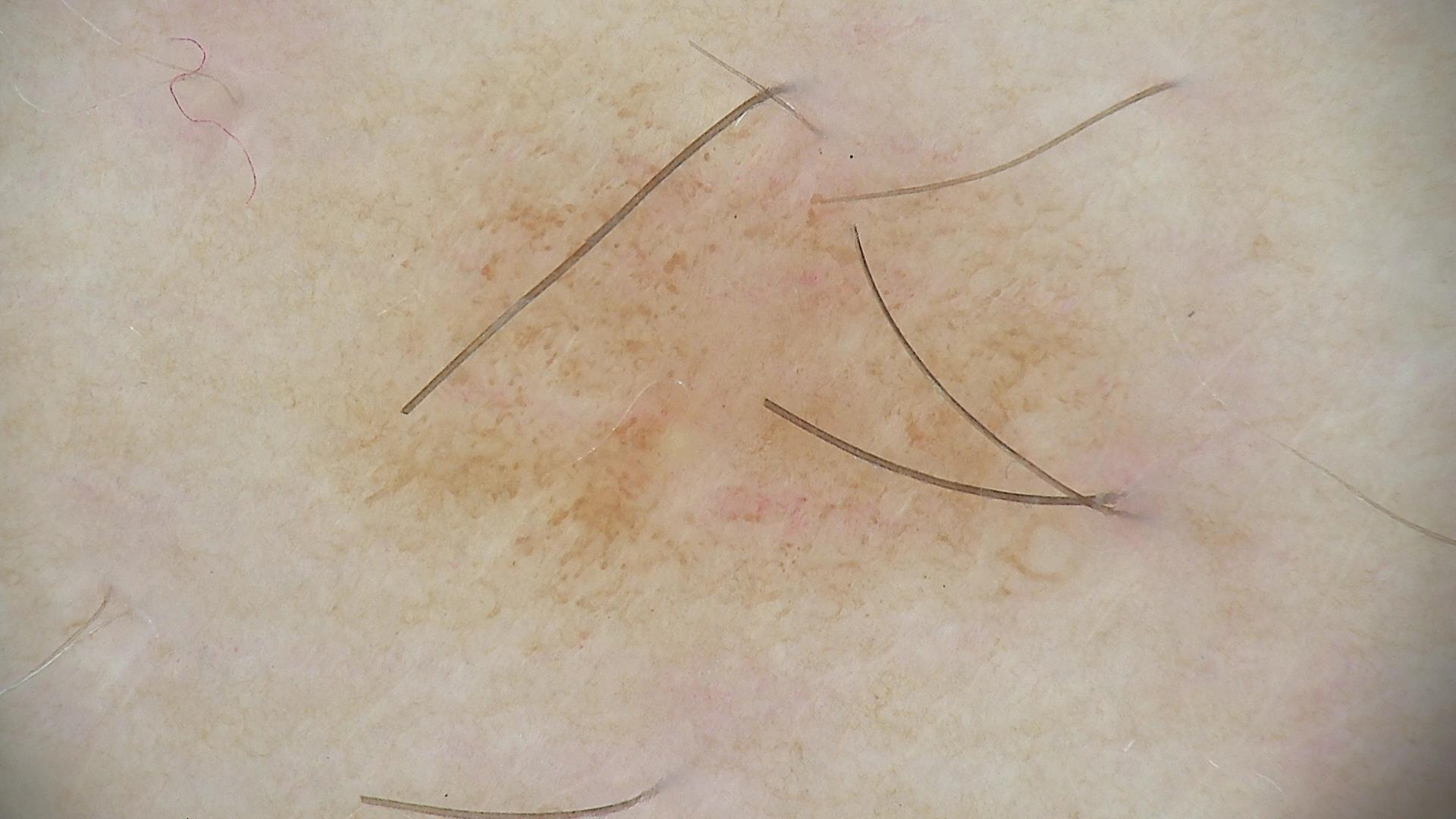{"diagnosis": {"name": "dysplastic junctional nevus", "code": "jd", "malignancy": "benign", "super_class": "melanocytic", "confirmation": "expert consensus"}}